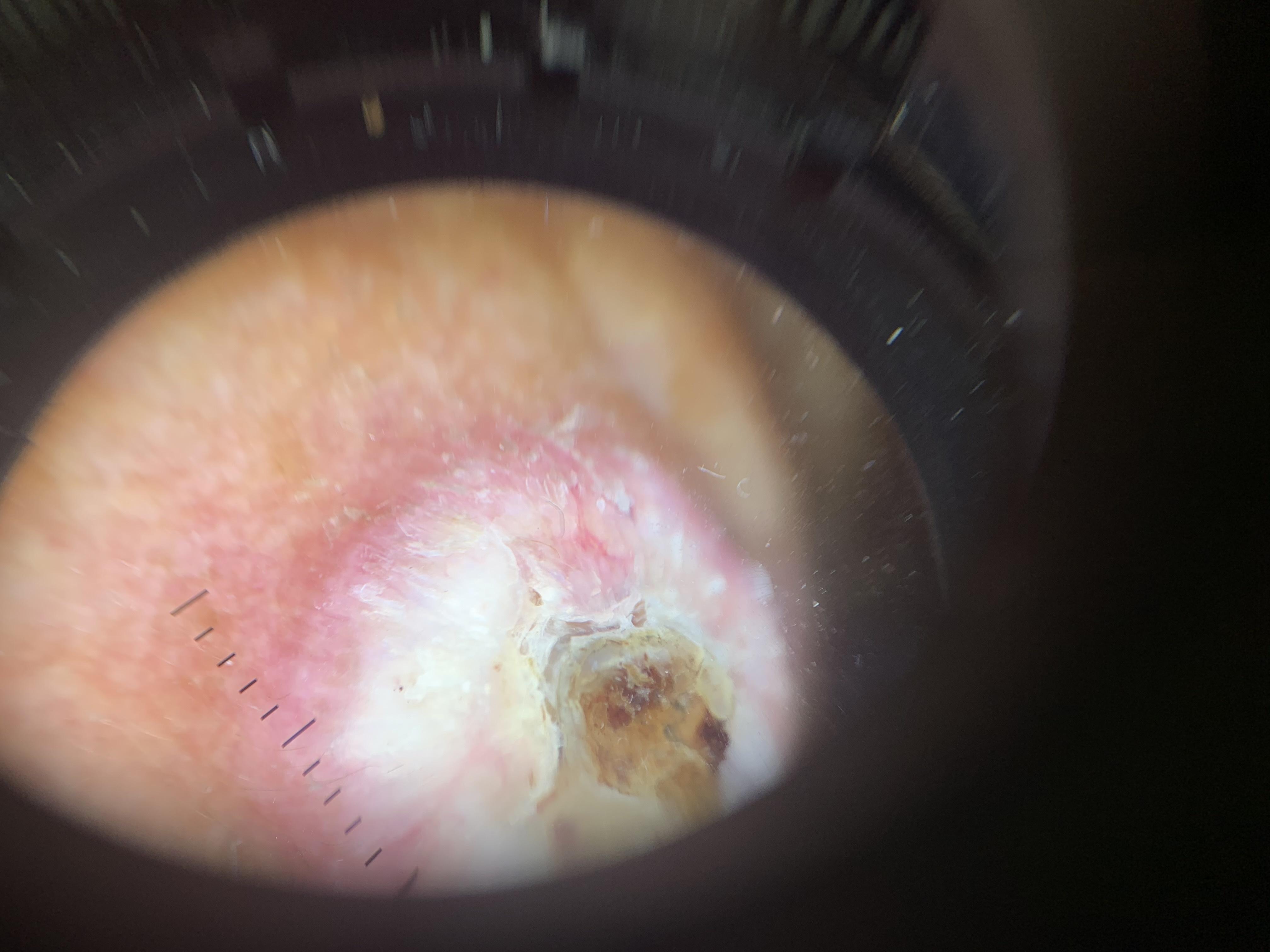Notes:
– modality: dermoscopy
– location: the head or neck
– pathology: Squamous cell carcinoma (biopsy-proven)